The affected area is the top or side of the foot · this image was taken at a distance:
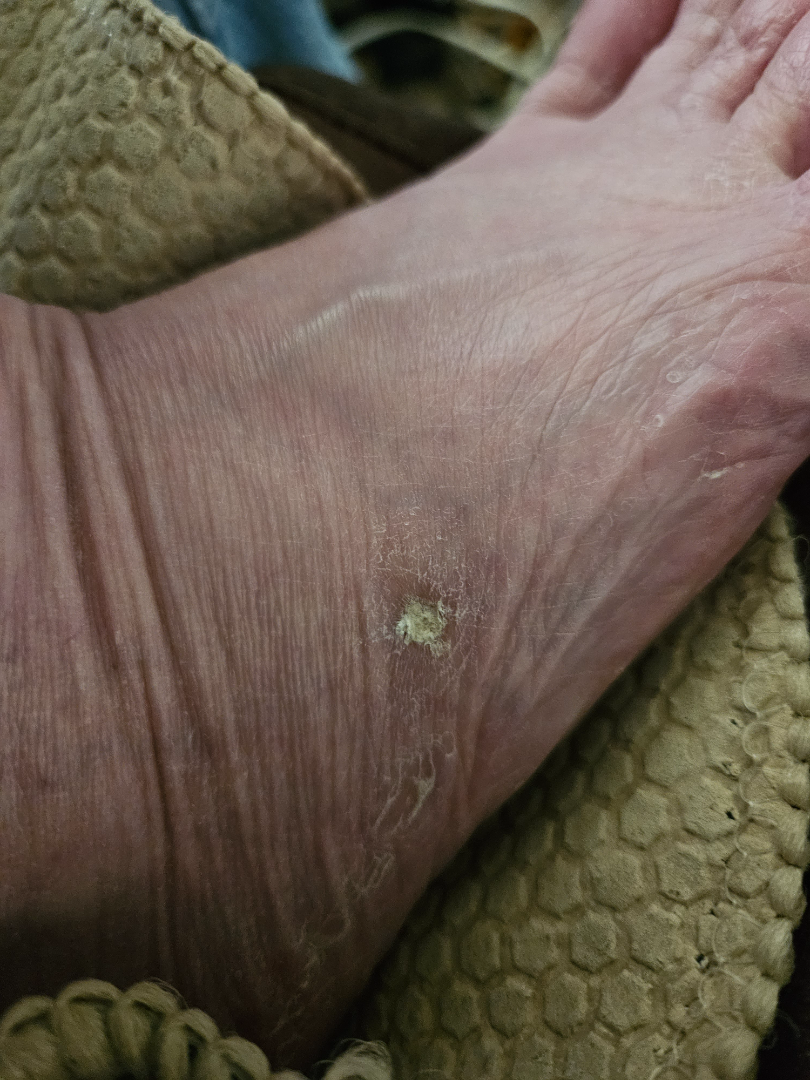assessment: not assessable